A dermoscopic photograph of a skin lesion.
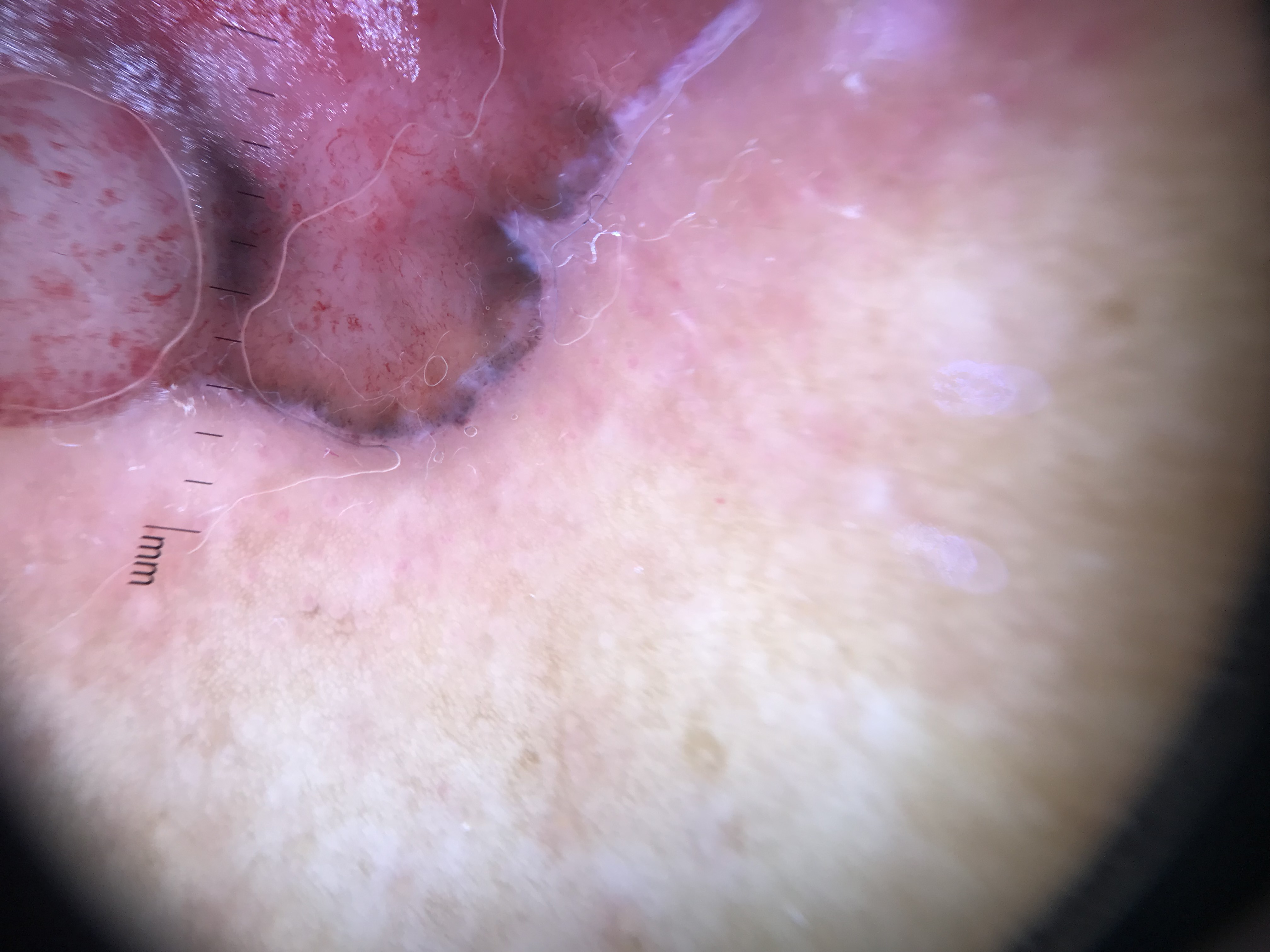classification=keratinocytic; diagnosis=basal cell carcinoma (biopsy-proven).